A close-up photograph:
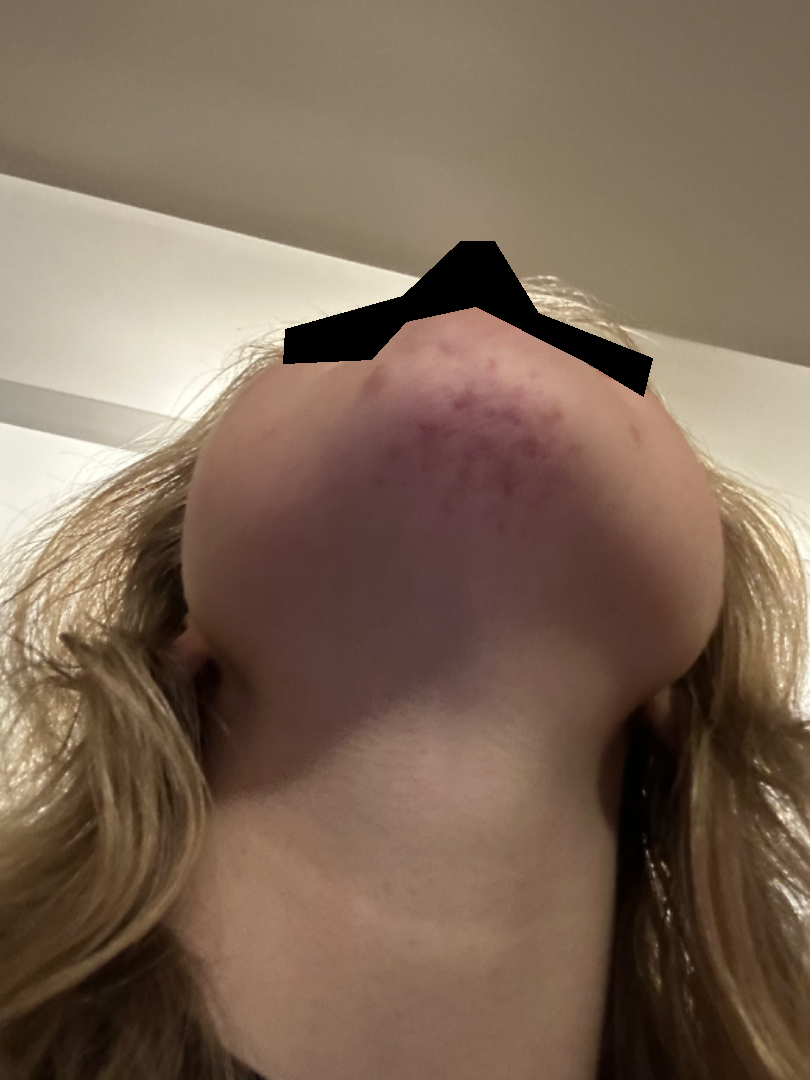Case summary:
• impression — most consistent with Acne